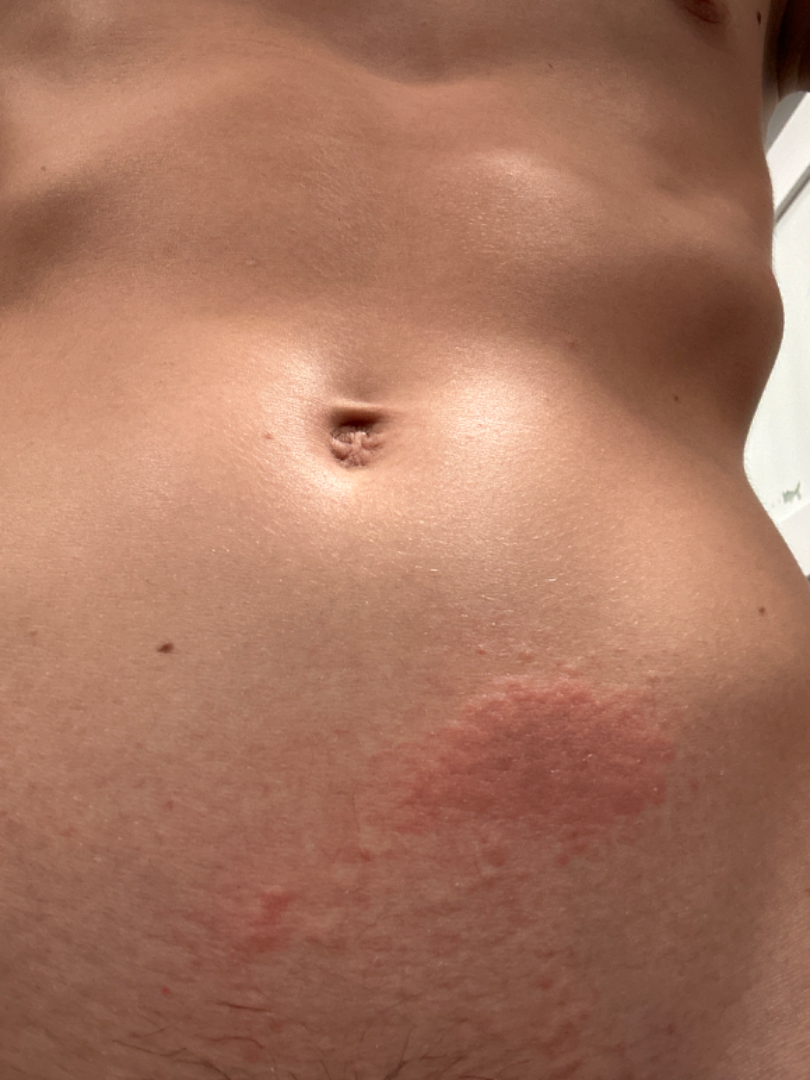* anatomic site · head or neck, leg and arm
* patient · male, age 18–29
* self-categorized as · a rash
* image framing · at a distance
* texture · raised or bumpy
* skin tone · FST II
* differential diagnosis · the leading impression is Urticaria; with consideration of Acute dermatitis, NOS; less probable is Allergic Contact Dermatitis; less likely is Eczema